A smartphone photograph of a skin lesion; a male patient in their early 60s: 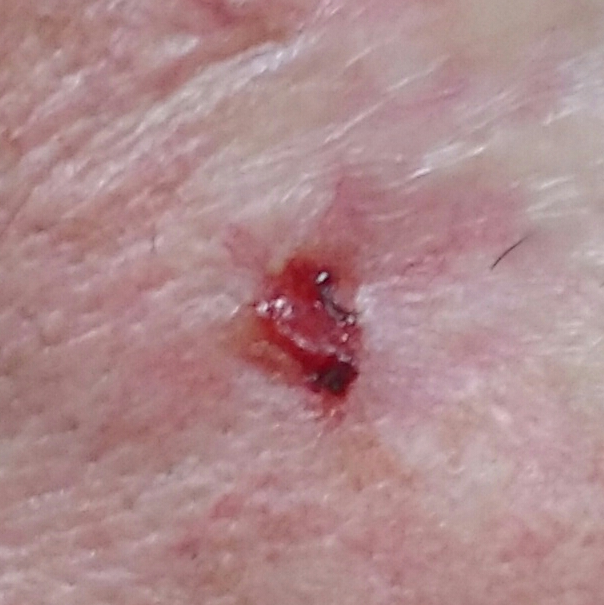Located on the face. The patient describes that the lesion has changed, hurts, has bled, itches, and has grown. On biopsy, the diagnosis was a basal cell carcinoma.